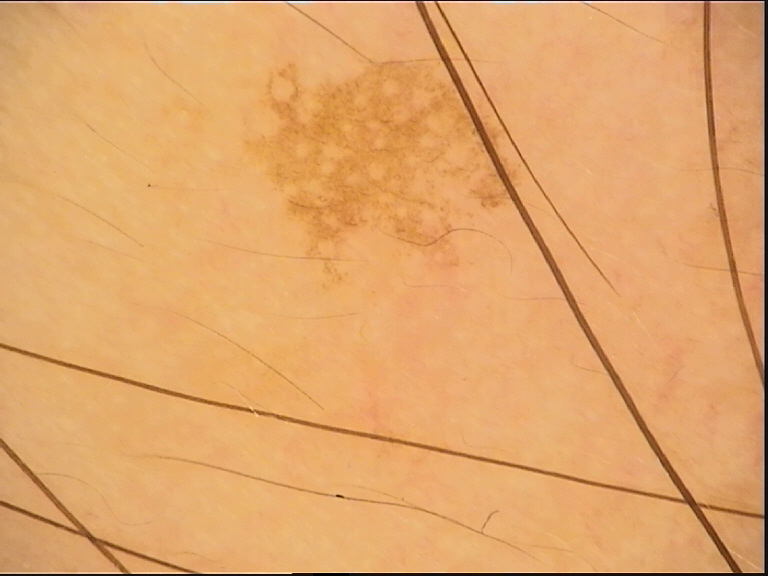Findings: A dermoscopic image of a skin lesion. Conclusion: Diagnosed as a benign lesion — a solar lentigo.